Female subject, age 18–29. A close-up photograph. The leg and top or side of the foot are involved. Reported duration is three to twelve months. The patient reports bothersome appearance, enlargement, darkening and itching. The patient reports the lesion is rough or flaky: 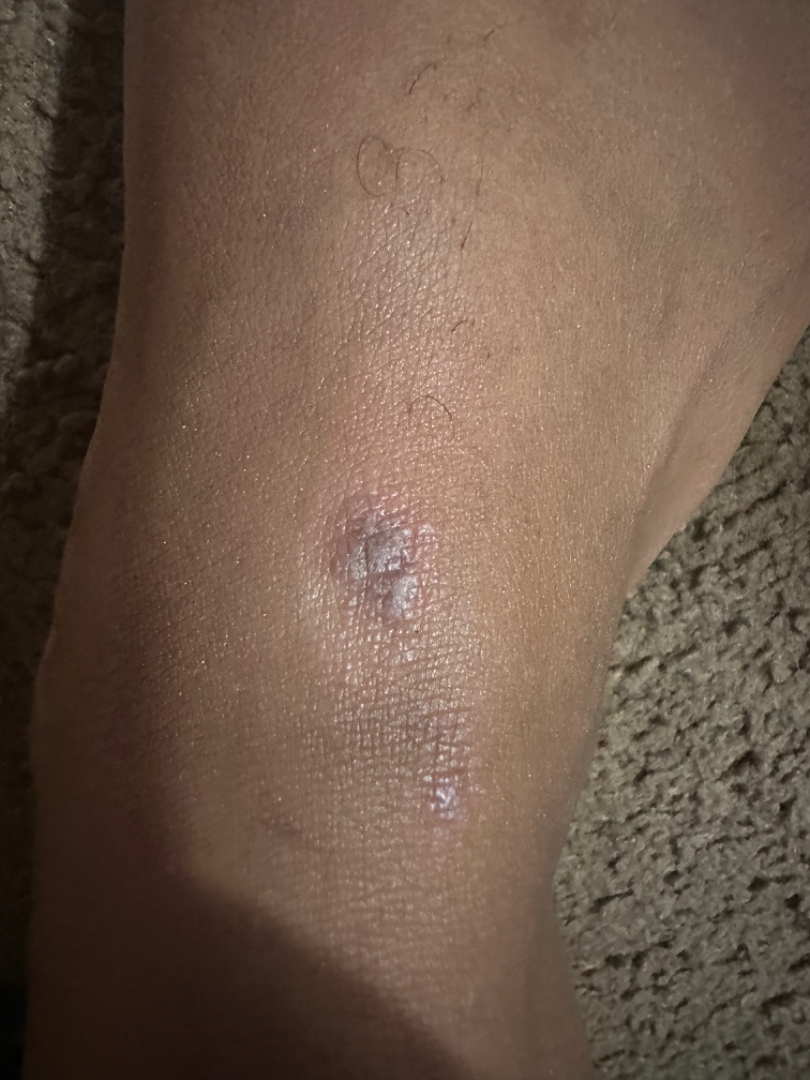* clinical impression — the differential, in no particular order, includes Lichen planus/lichenoid eruption, Lichen Simplex Chronicus and Insect Bite